A dermoscopic close-up of a skin lesion — 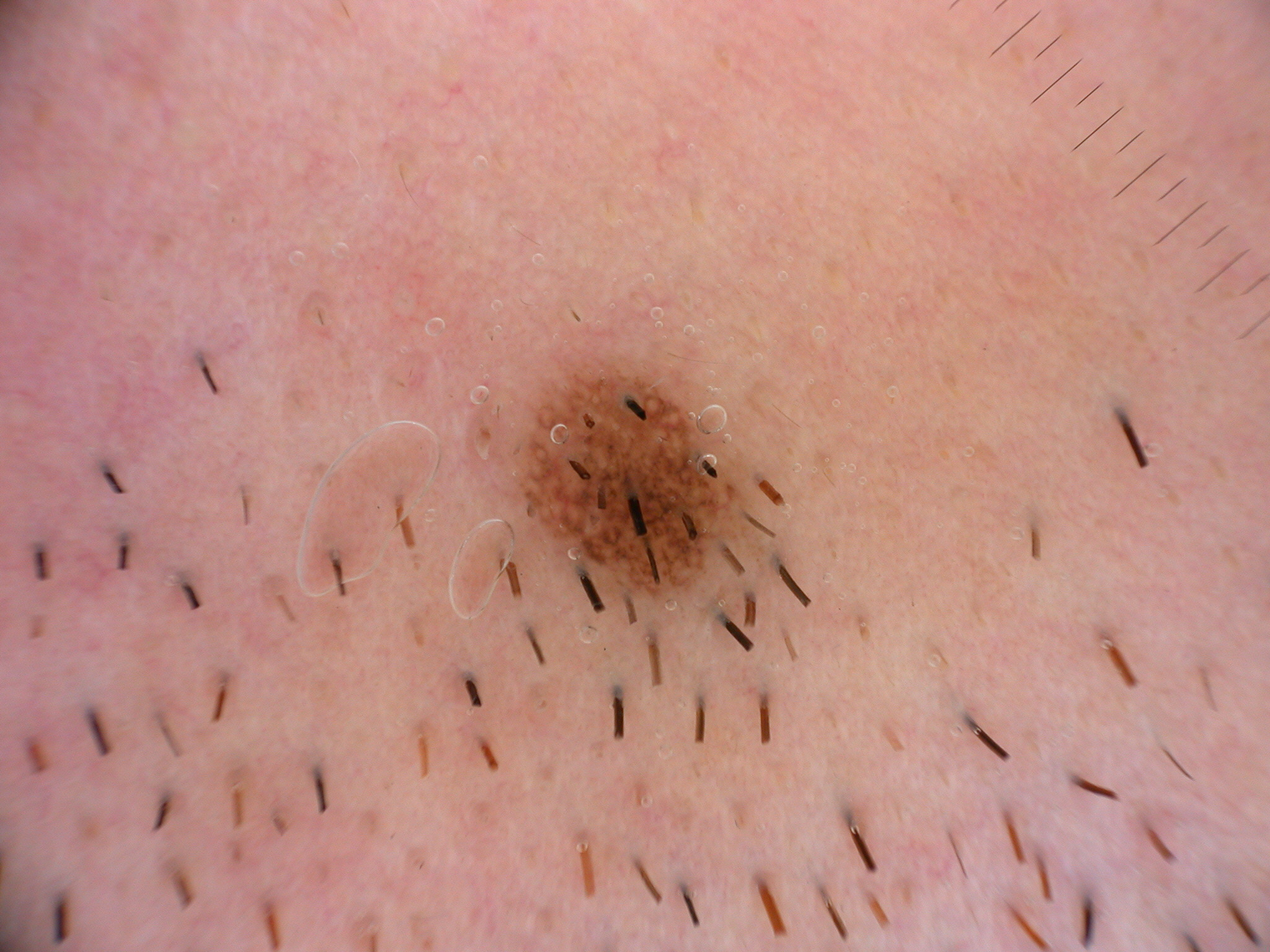<lesion>
<lesion_location>
  <bbox_xyxy>520, 371, 736, 594</bbox_xyxy>
</lesion_location>
<diagnosis>
  <name>melanocytic nevus</name>
  <malignancy>benign</malignancy>
  <lineage>melanocytic</lineage>
  <provenance>clinical</provenance>
</diagnosis>
</lesion>